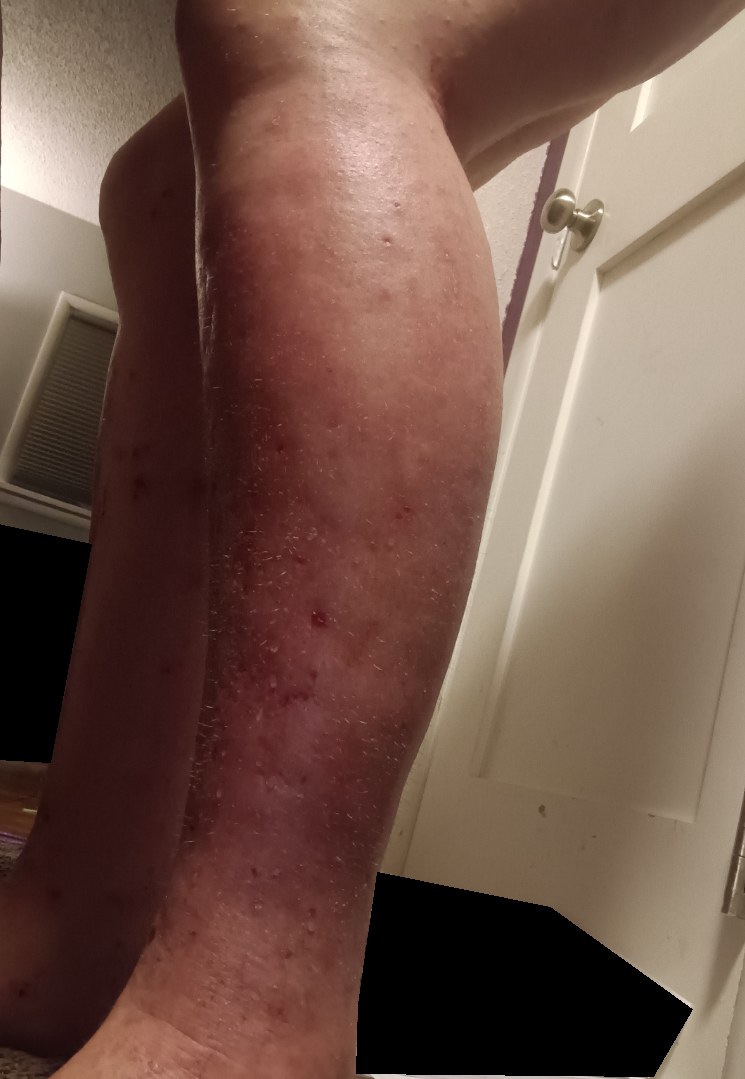- assessment: the leading consideration is Stasis Dermatitis; also raised was Cellulitis; also consider Eczema